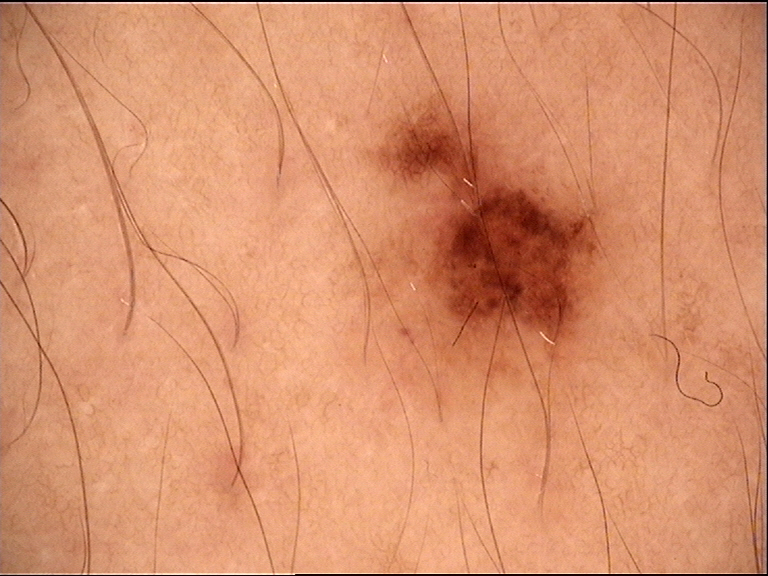label=dysplastic junctional nevus (expert consensus).